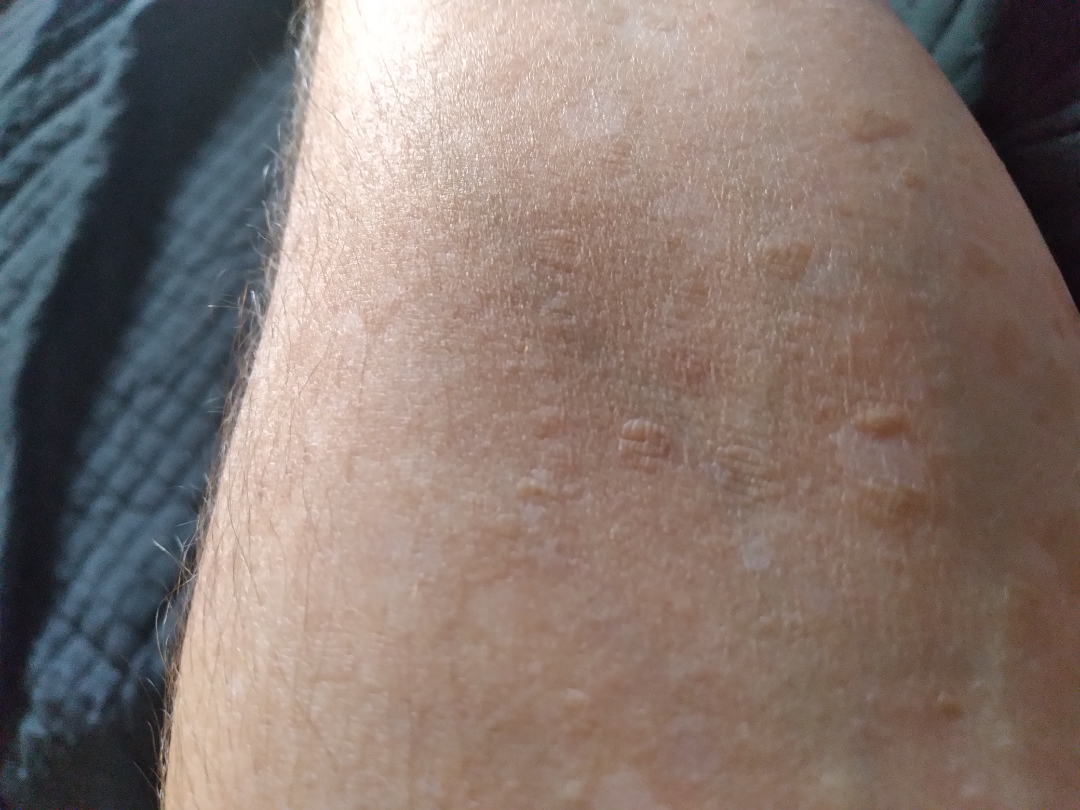The dermatologist could not determine a likely condition from the photograph alone. Located on the arm. The photograph is a close-up of the affected area. Texture is reported as raised or bumpy. The contributor notes the condition has been present for more than five years. The lesion is associated with bothersome appearance. No associated systemic symptoms reported. The contributor is 40–49, male.